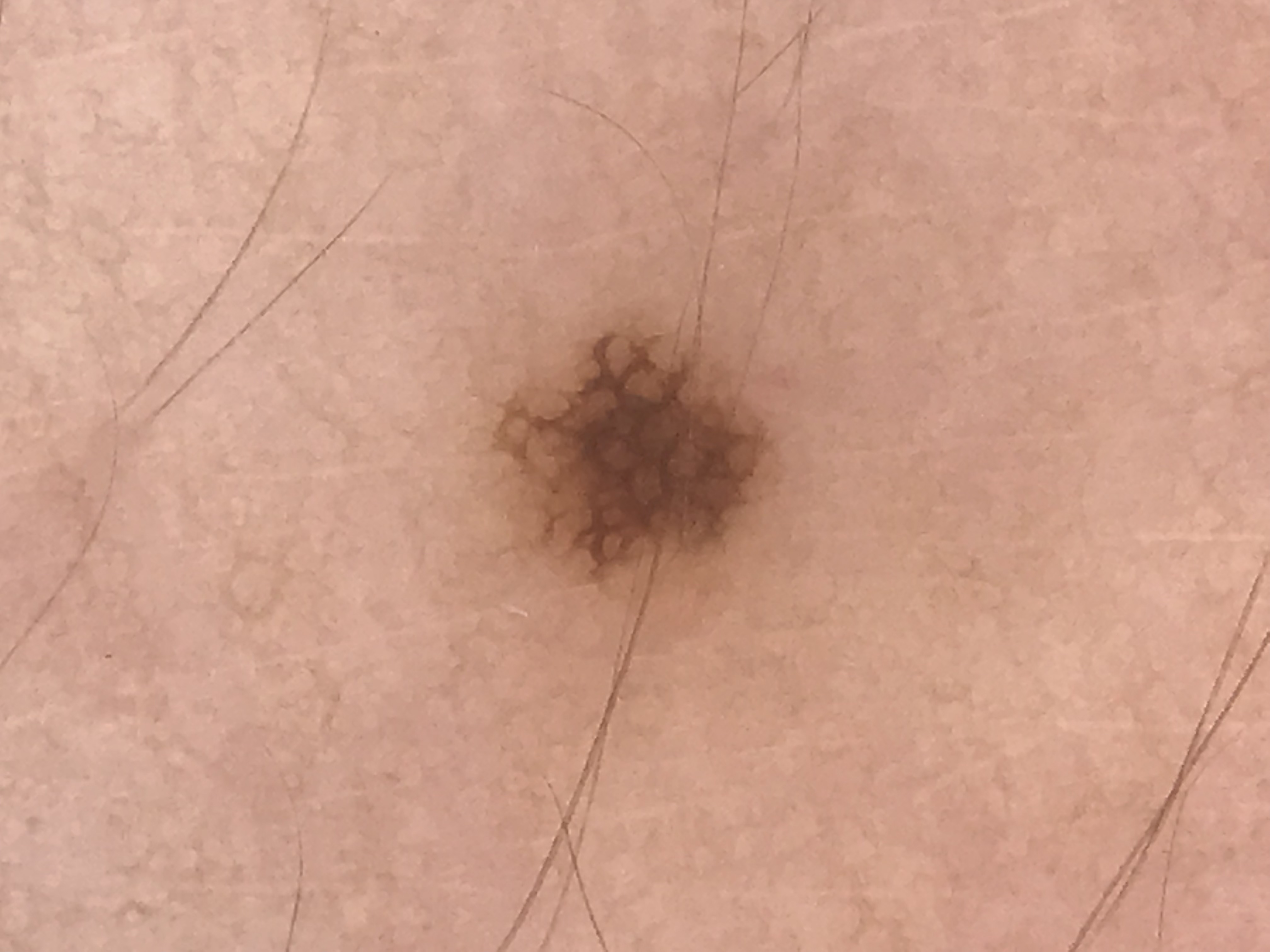The diagnosis was a junctional nevus.